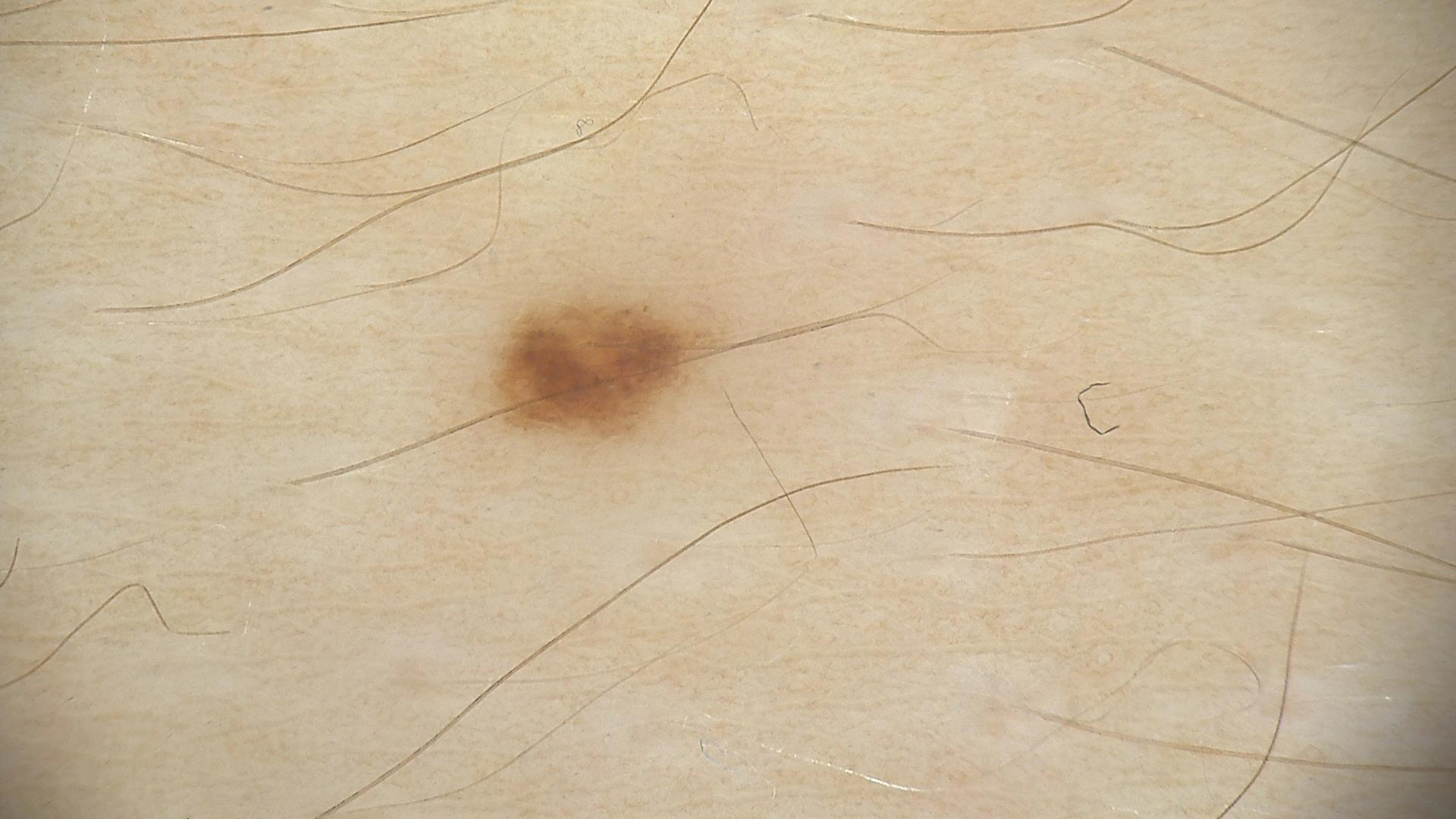assessment = dysplastic junctional nevus (expert consensus).